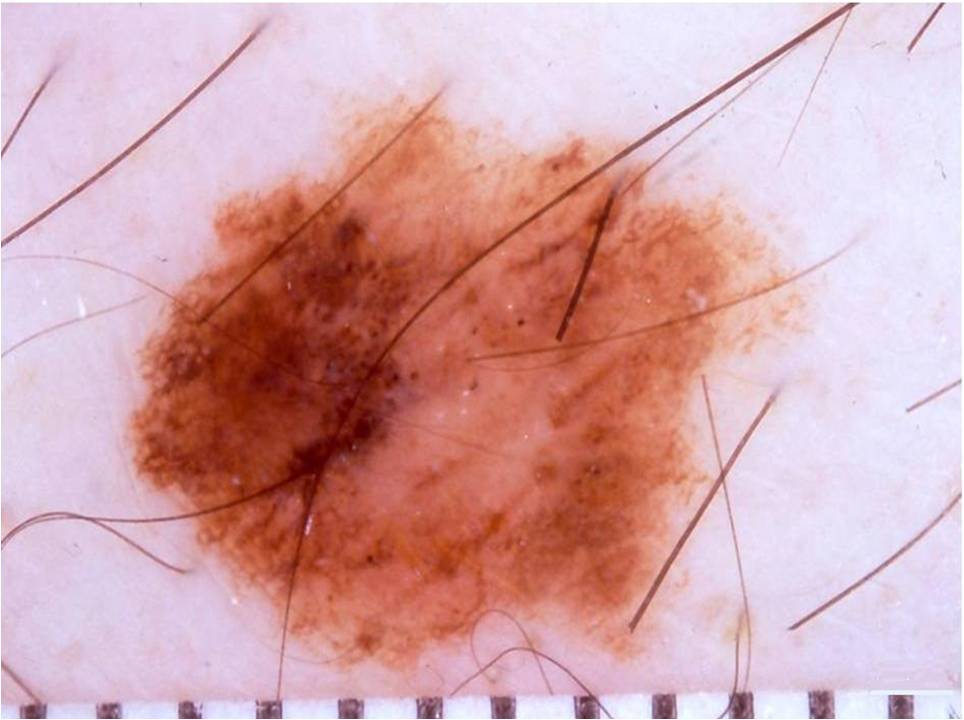patient = male, aged 43-47
modality = dermoscopy of a skin lesion
extent = ~41% of the field
location = x1=116 y1=71 x2=818 y2=676
dermoscopic findings = globules and pigment network; absent: milia-like cysts, negative network, and streaks
impression = a melanoma, a malignant skin lesion